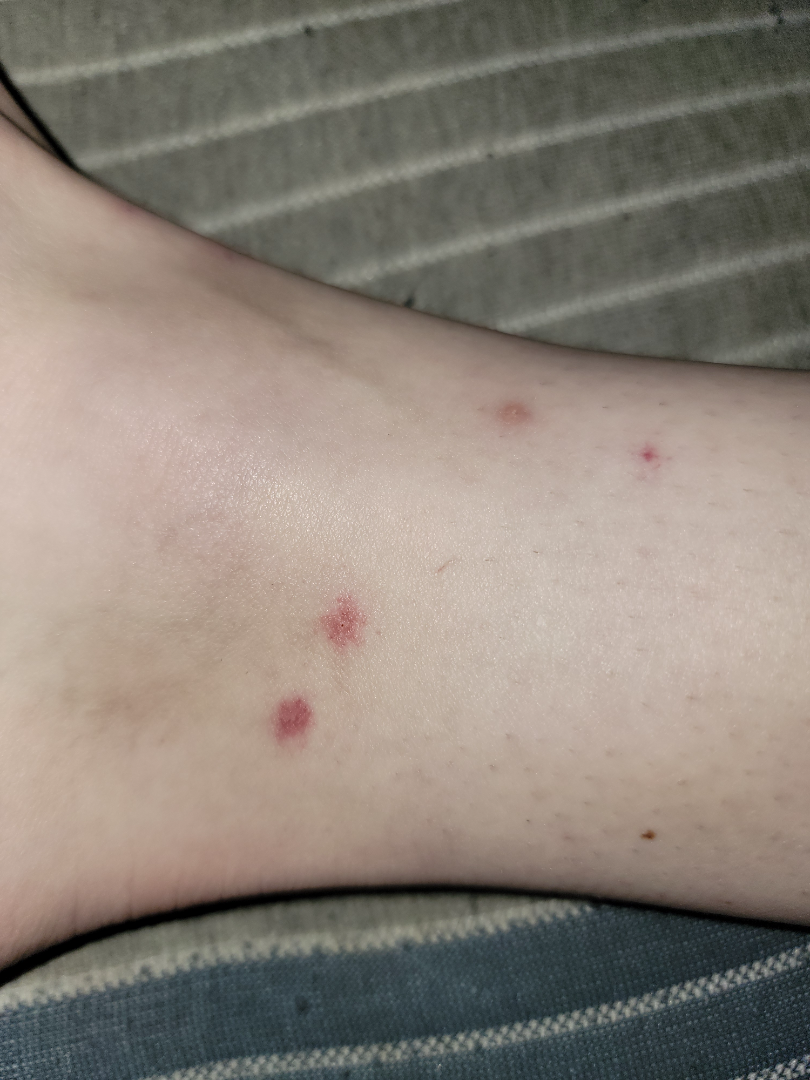assessment = could not be assessed, symptoms = bothersome appearance, shot type = close-up, body site = top or side of the foot and leg, surface texture = flat, duration = about one day.